This is a close-up image, texture is reported as raised or bumpy, the arm is involved, the patient considered this a rash, the subject is a female aged 40–49, the contributor reports the condition has been present for one to four weeks — 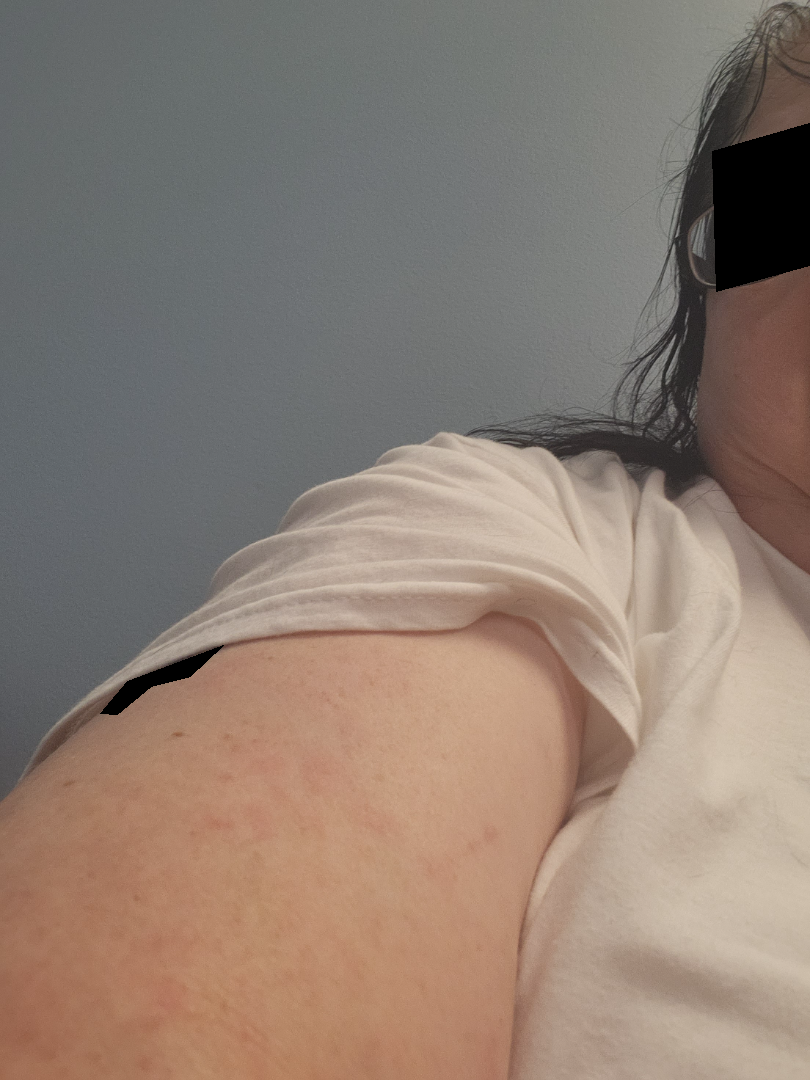assessment: unable to determine